Texture is reported as rough or flaky, fluid-filled and raised or bumpy. The patient described the issue as a rash. Symptoms reported: bothersome appearance. The condition has been present for more than five years. The photo was captured at an angle. The patient notes associated fatigue, joint pain, shortness of breath and fever. The lesion involves the arm, back of the hand, head or neck, leg, back of the torso, front of the torso, top or side of the foot, sole of the foot and palm — 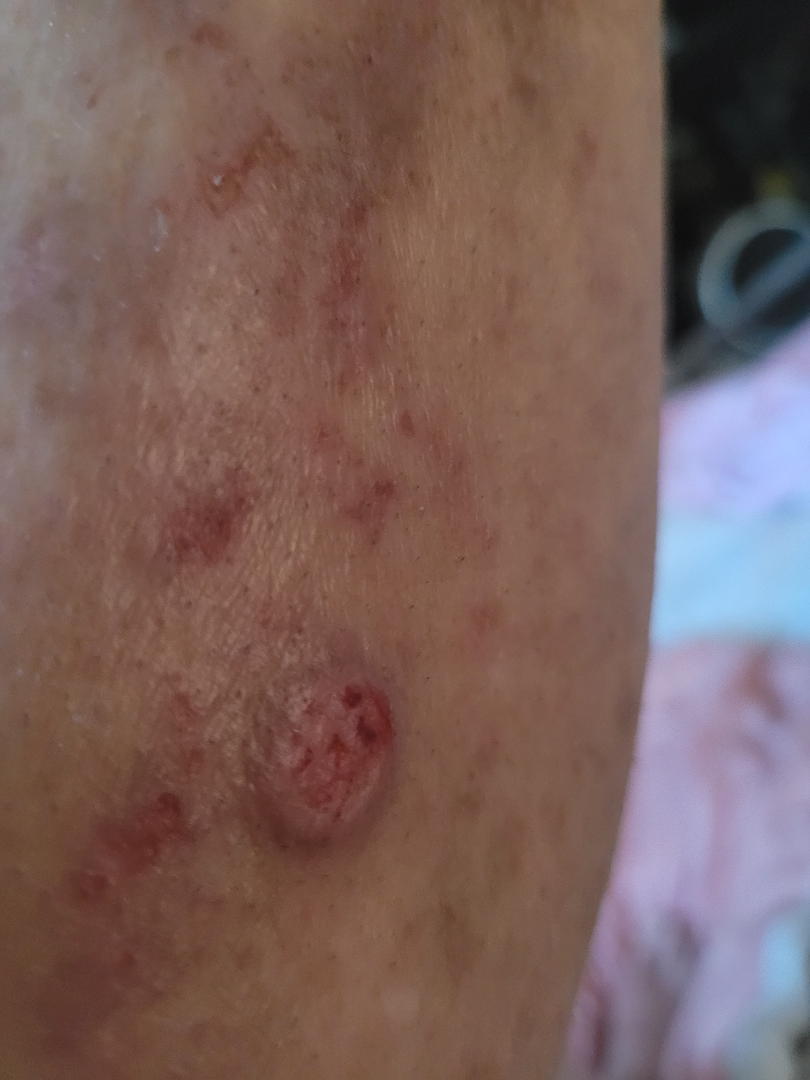Impression: No differential diagnosis could be assigned on photographic review.